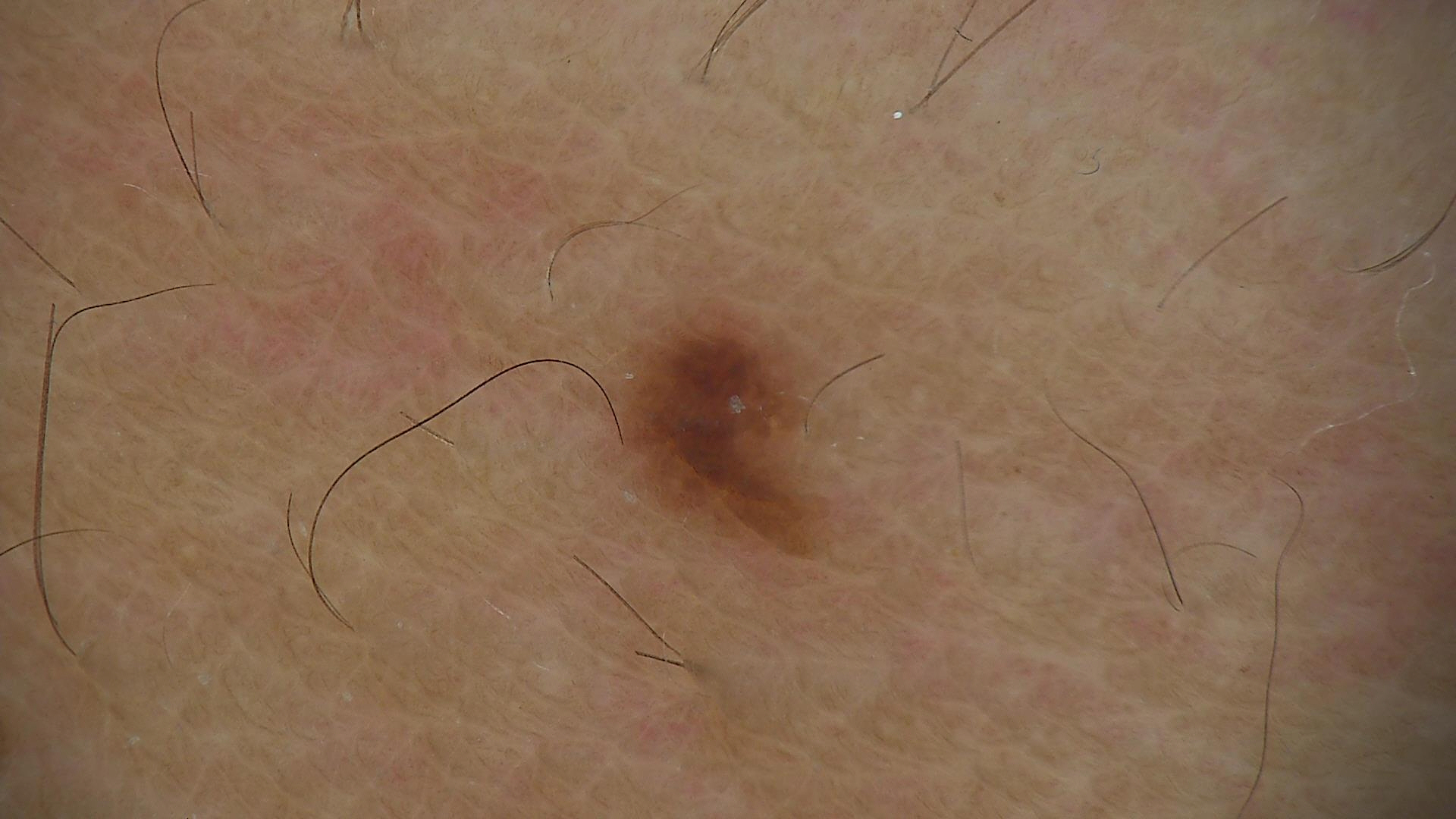image type: dermatoscopy | diagnostic label: dysplastic junctional nevus (expert consensus).